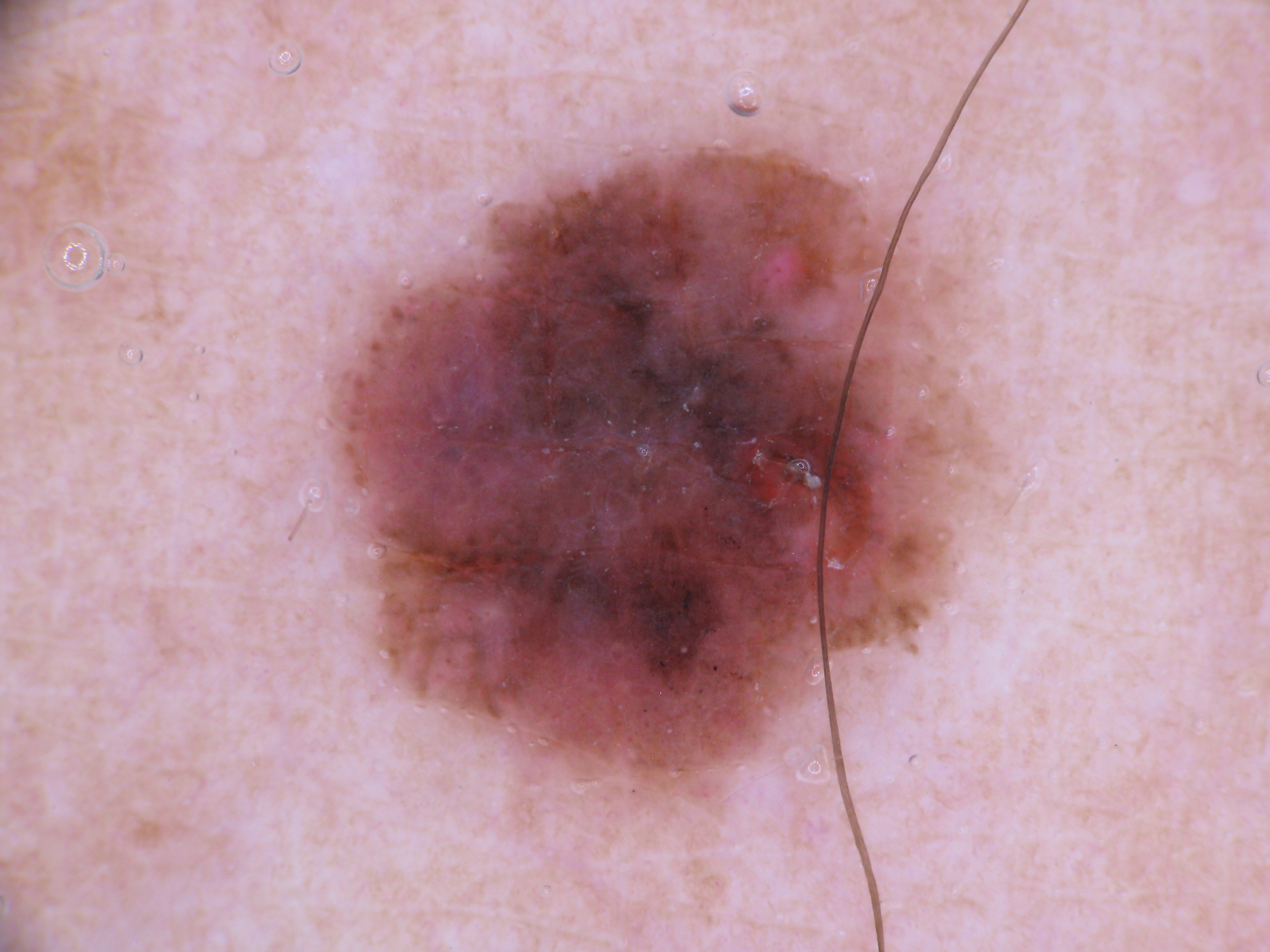A dermoscopy image of a single skin lesion. In (x1, y1, x2, y2) order, the lesion occupies the region (322, 145, 970, 796). Dermoscopy demonstrates pigment network and globules. Histopathology confirmed a melanoma, a skin cancer.